The patient says their skin tans without first burning; a dermatoscopic image of a skin lesion; acquired for a research image collection, with no referral diagnosis; the patient describes having few moles overall — 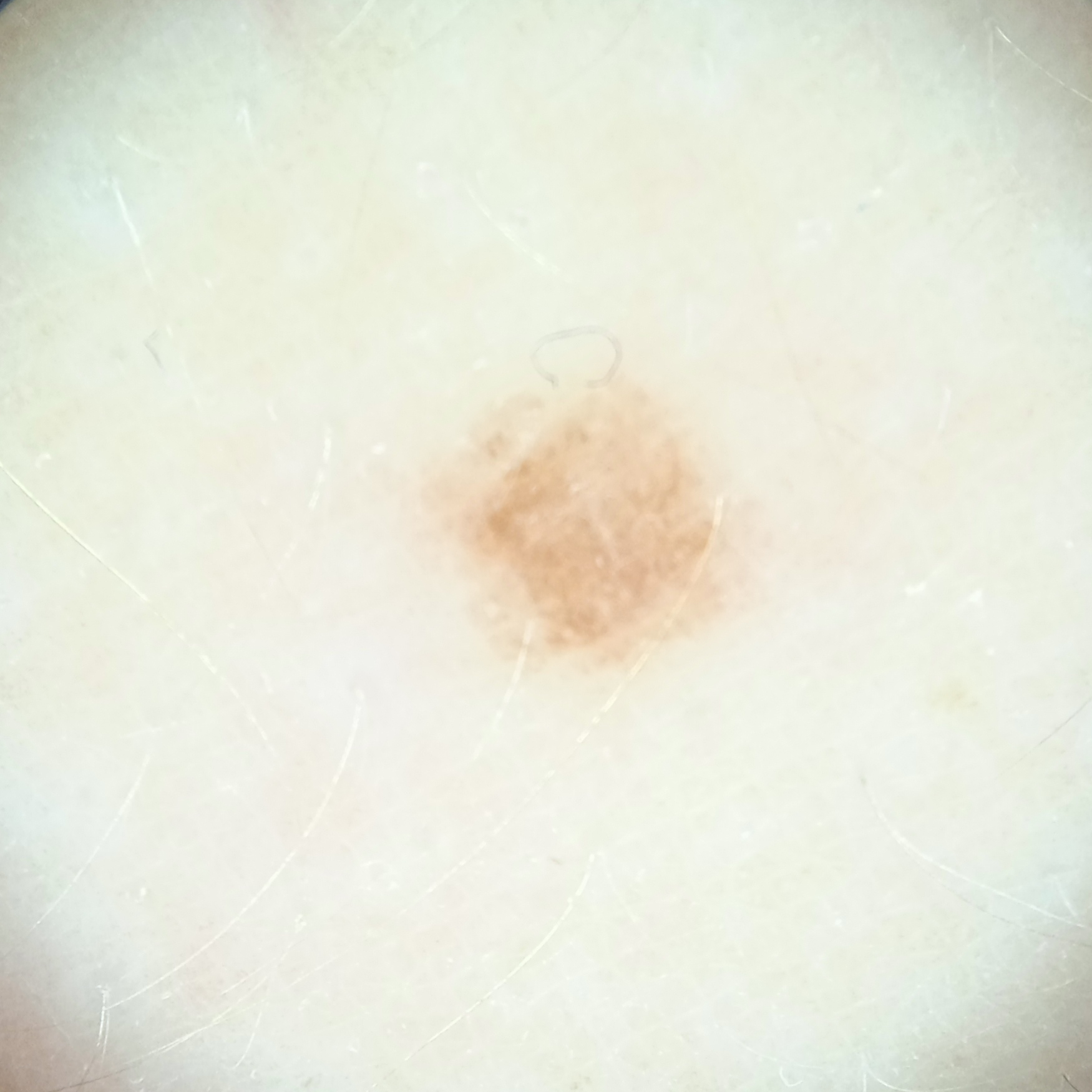Q: Where is the lesion?
A: an arm
Q: Lesion size?
A: 3.5 mm
Q: What was the diagnosis?
A: melanocytic nevus (dermatologist consensus)